History notes pesticide exposure and tobacco use. A male patient aged 66. FST II. A clinical photo of a skin lesion taken with a smartphone.
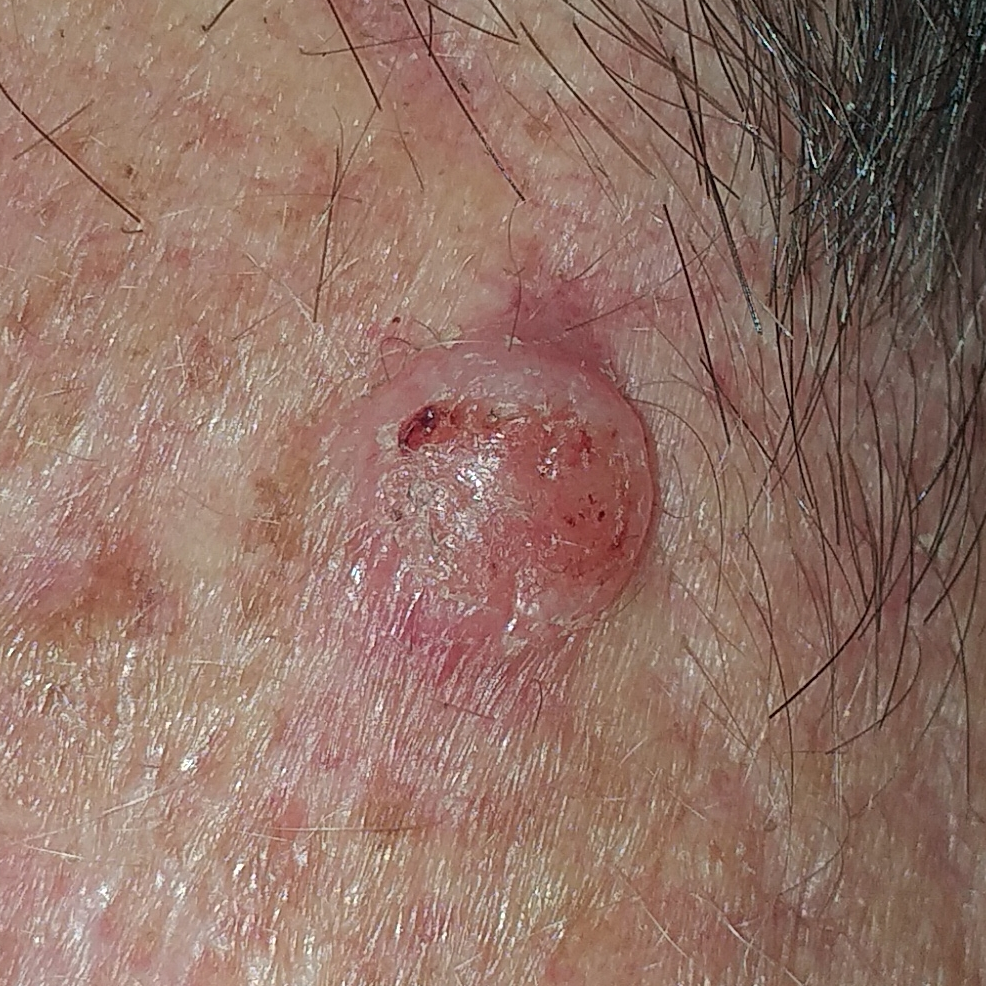{
  "lesion_location": "the neck",
  "lesion_size": {
    "diameter_1_mm": 8.0,
    "diameter_2_mm": 6.0
  },
  "symptoms": {
    "present": [
      "itching",
      "elevation",
      "bleeding"
    ]
  },
  "diagnosis": {
    "name": "basal cell carcinoma",
    "code": "BCC",
    "malignancy": "malignant",
    "confirmation": "histopathology"
  }
}